The photograph was taken at a distance; the subject is a male aged 18–29 — 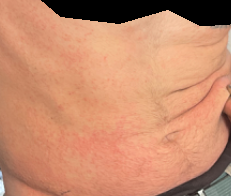Q: What conditions are considered?
A: one reviewing dermatologist: the favored diagnosis is Drug Rash; also raised was Viral Exanthem; a remote consideration is Hypersensitivity